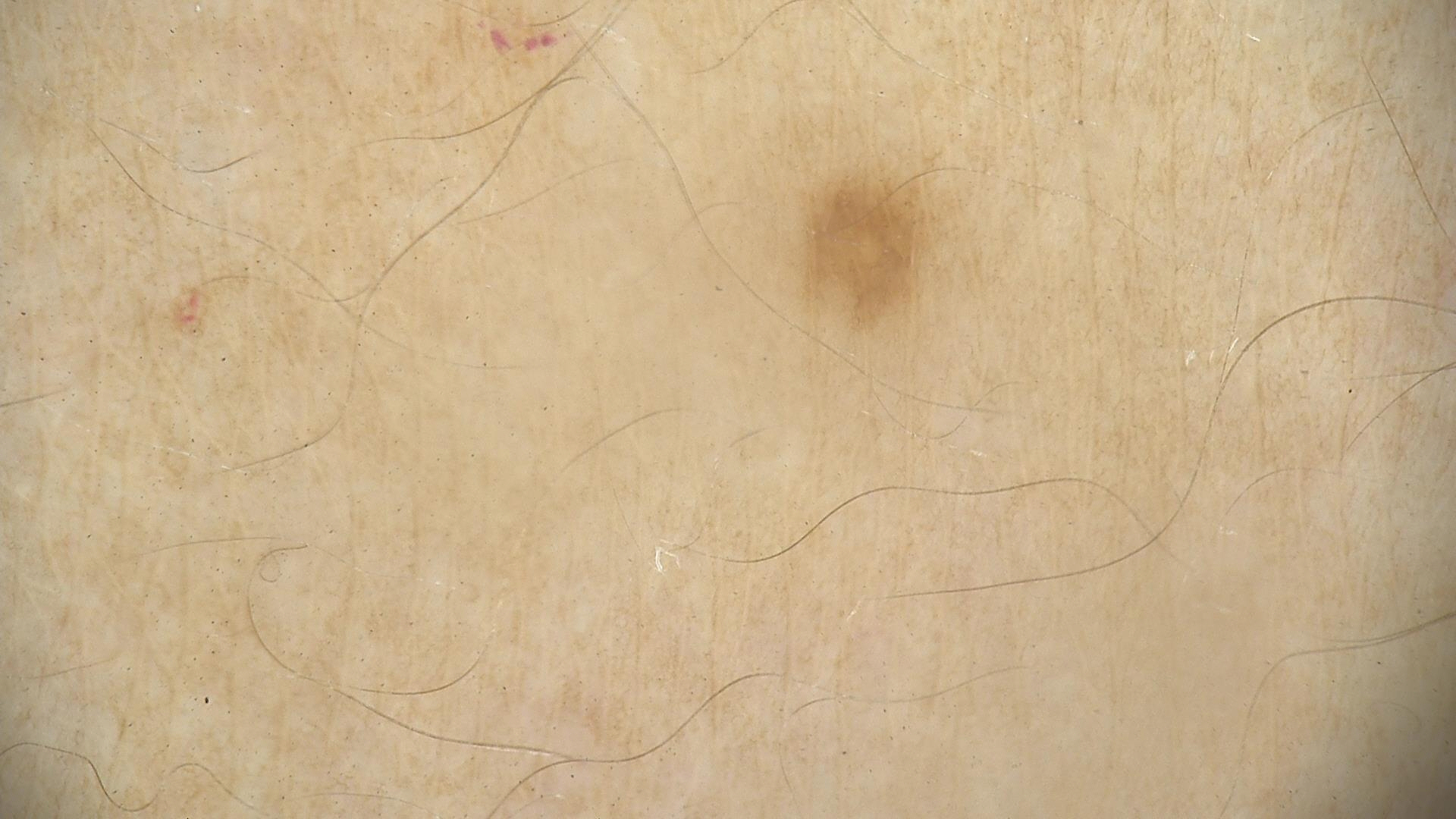Consistent with a lentigo simplex.